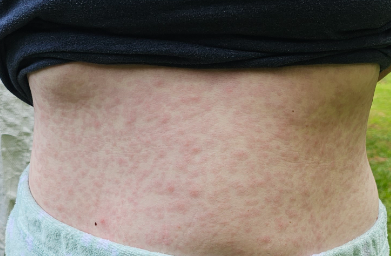Findings:
The case was difficult to assess from the available photograph.